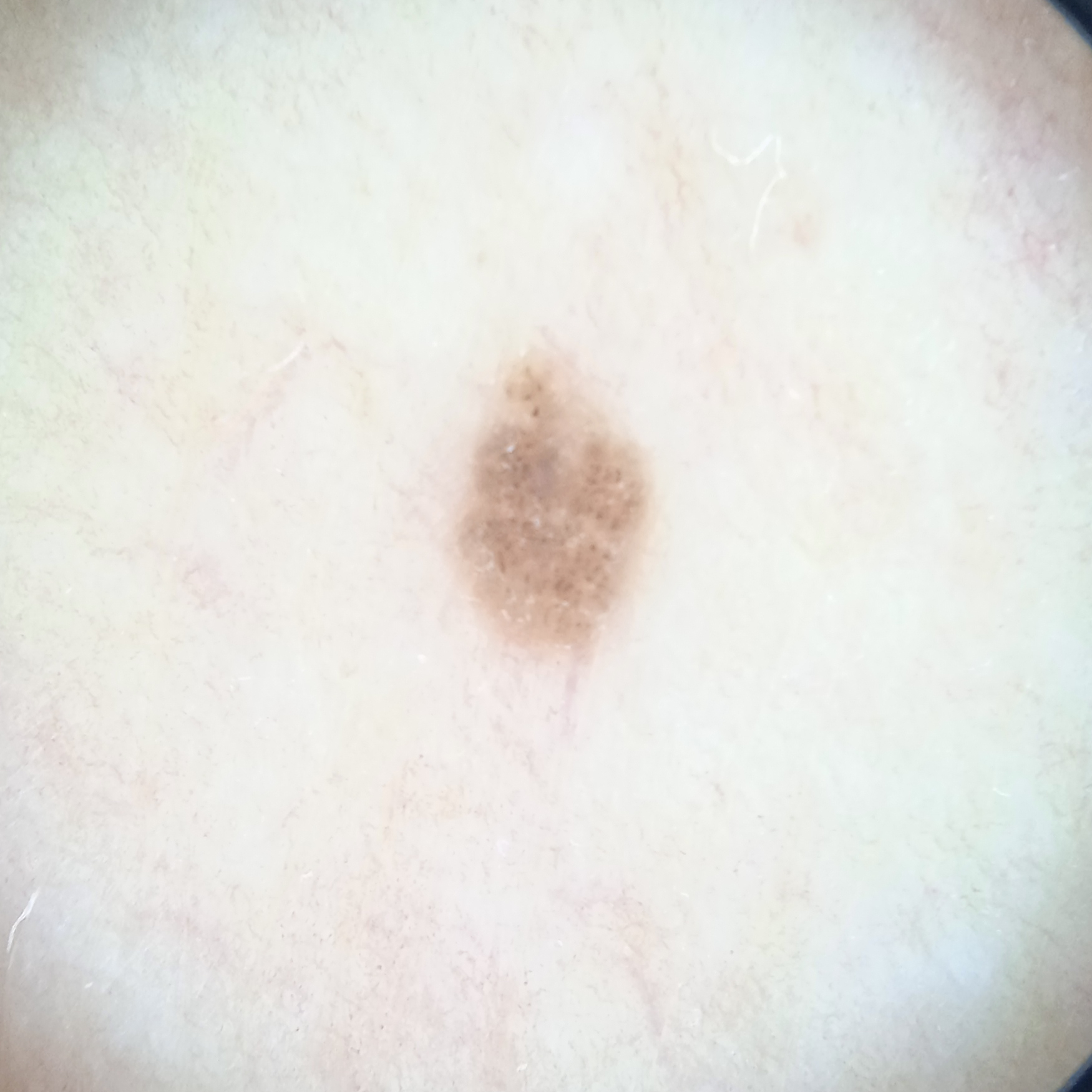{
  "referral": "research study (no referral diagnosis)",
  "patient": {
    "age": 60,
    "sex": "female"
  },
  "image": "dermoscopy",
  "lesion_location": "the torso",
  "diagnosis": {
    "name": "melanocytic nevus",
    "malignancy": "benign"
  }
}